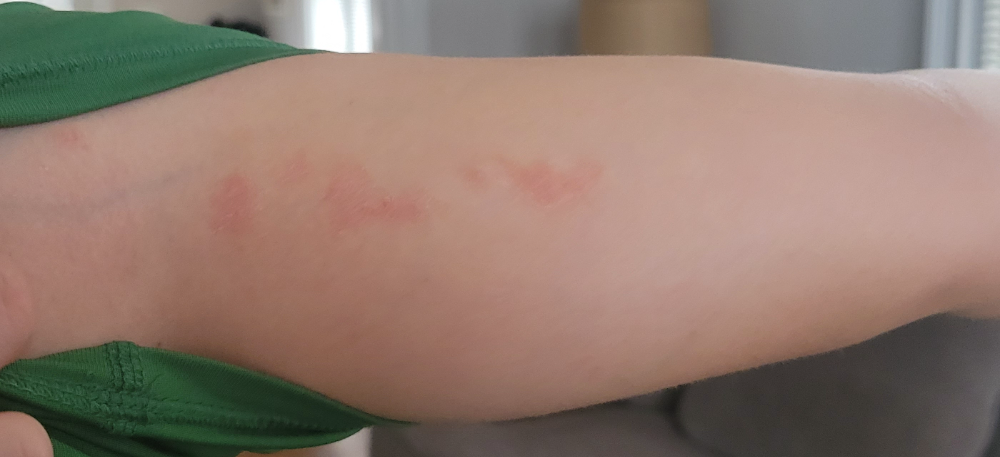The case was indeterminate on photographic review. The photo was captured at a distance. The contributor is a male aged 18–29. The patient indicates the condition has been present for less than one week. No relevant systemic symptoms. The patient indicates the lesion is rough or flaky and raised or bumpy. The patient reported no relevant symptoms from the lesion. Located on the arm.